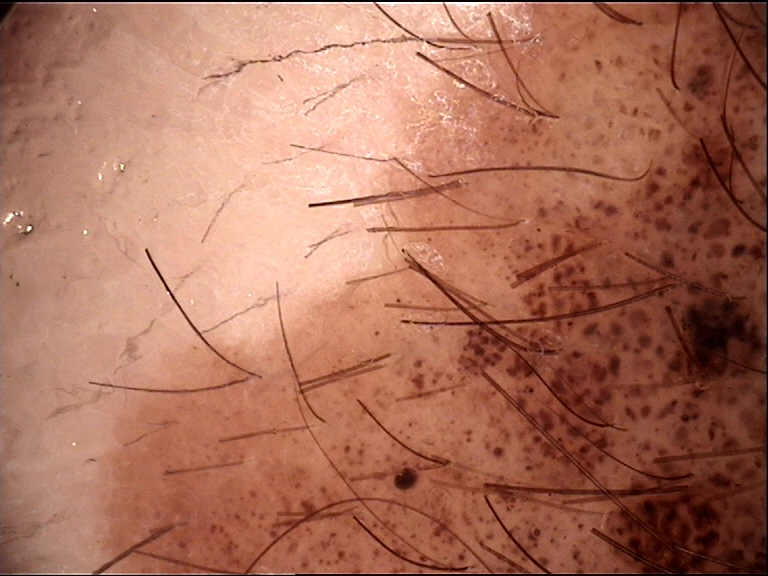The diagnostic label was a banal lesion — a congenital compound nevus.